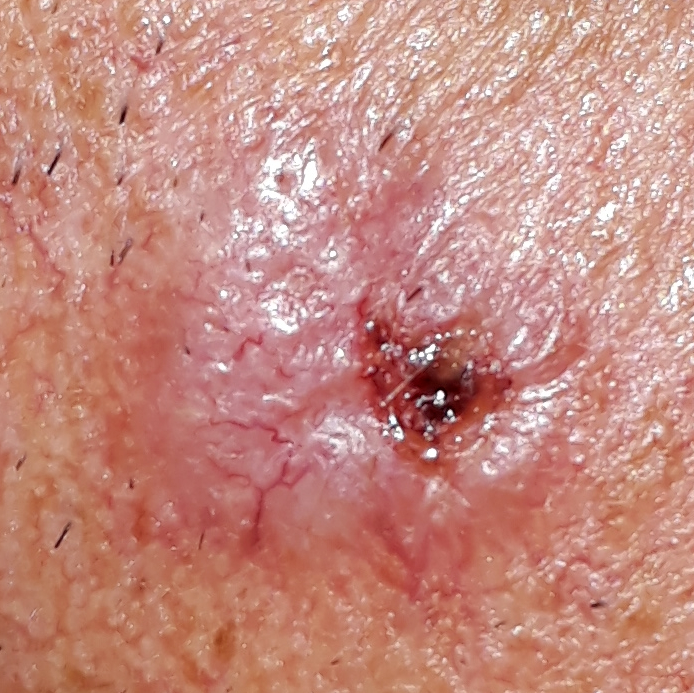| field | value |
|---|---|
| subject | male, in their 40s |
| risk factors | prior skin cancer (patient or family), pesticide exposure |
| imaging | clinical photo |
| FST | II |
| body site | the face |
| diameter | approx. 15 × 14 mm |
| symptoms | itching, bleeding, growth, elevation |
| diagnostic label | basal cell carcinoma (biopsy-proven) |